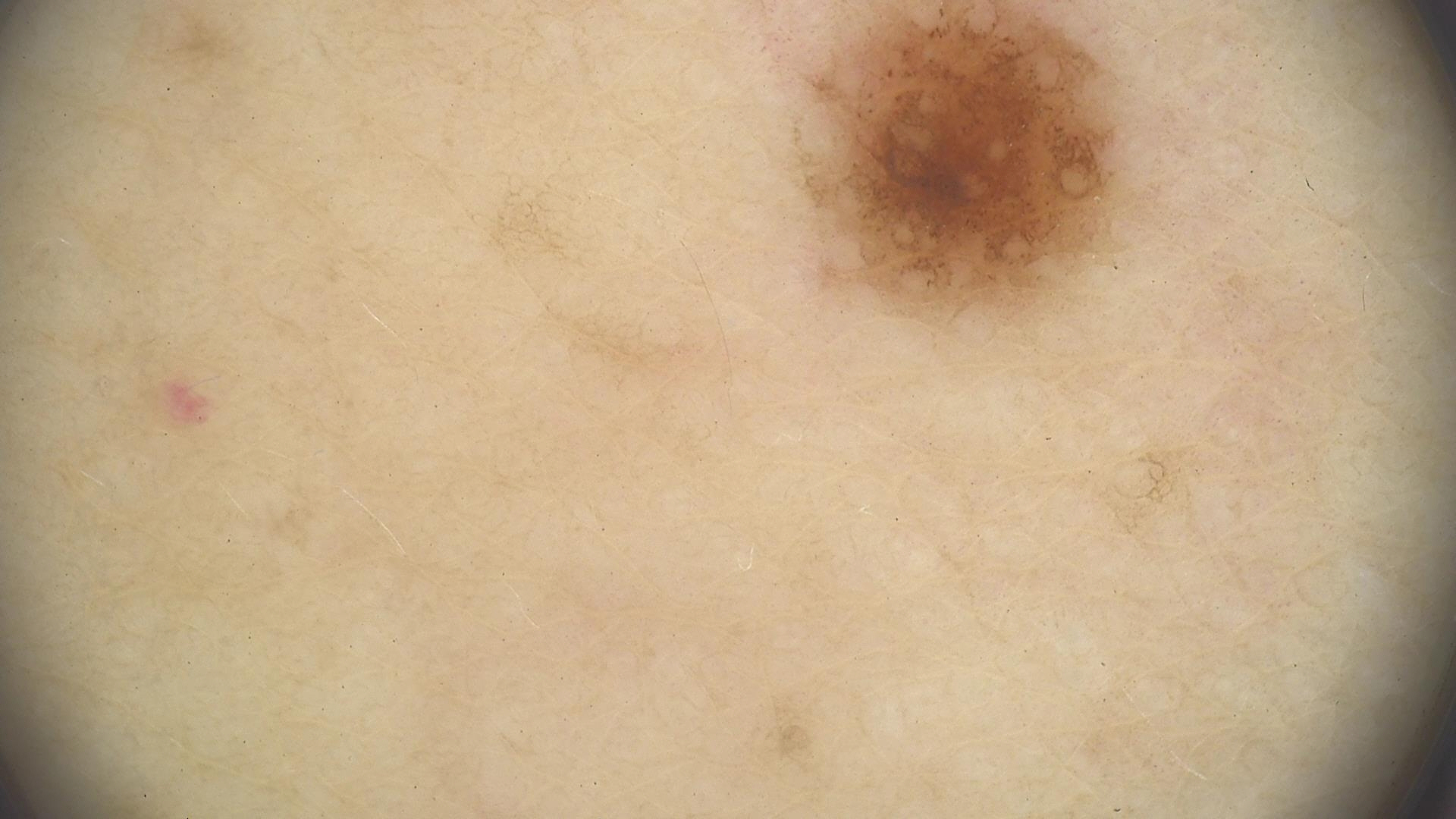Impression: The diagnosis was a dysplastic junctional nevus.